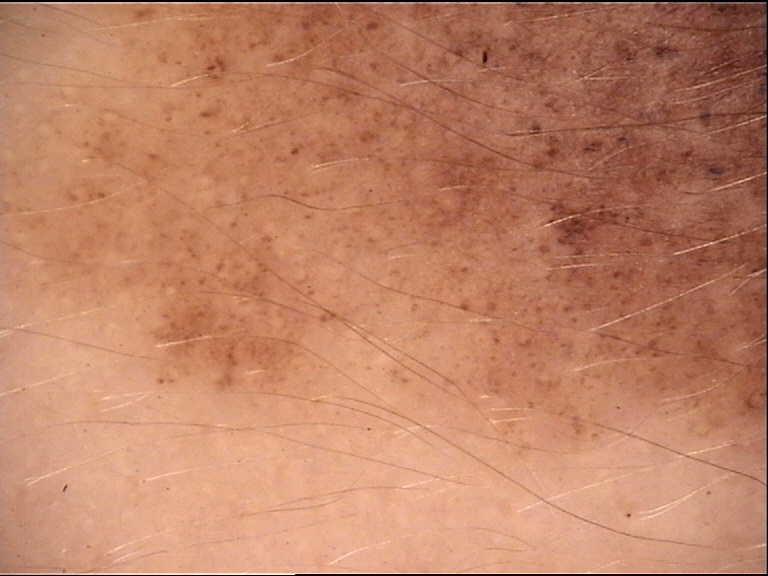assessment: congenital junctional nevus (expert consensus).